A skin lesion imaged with a dermatoscope.
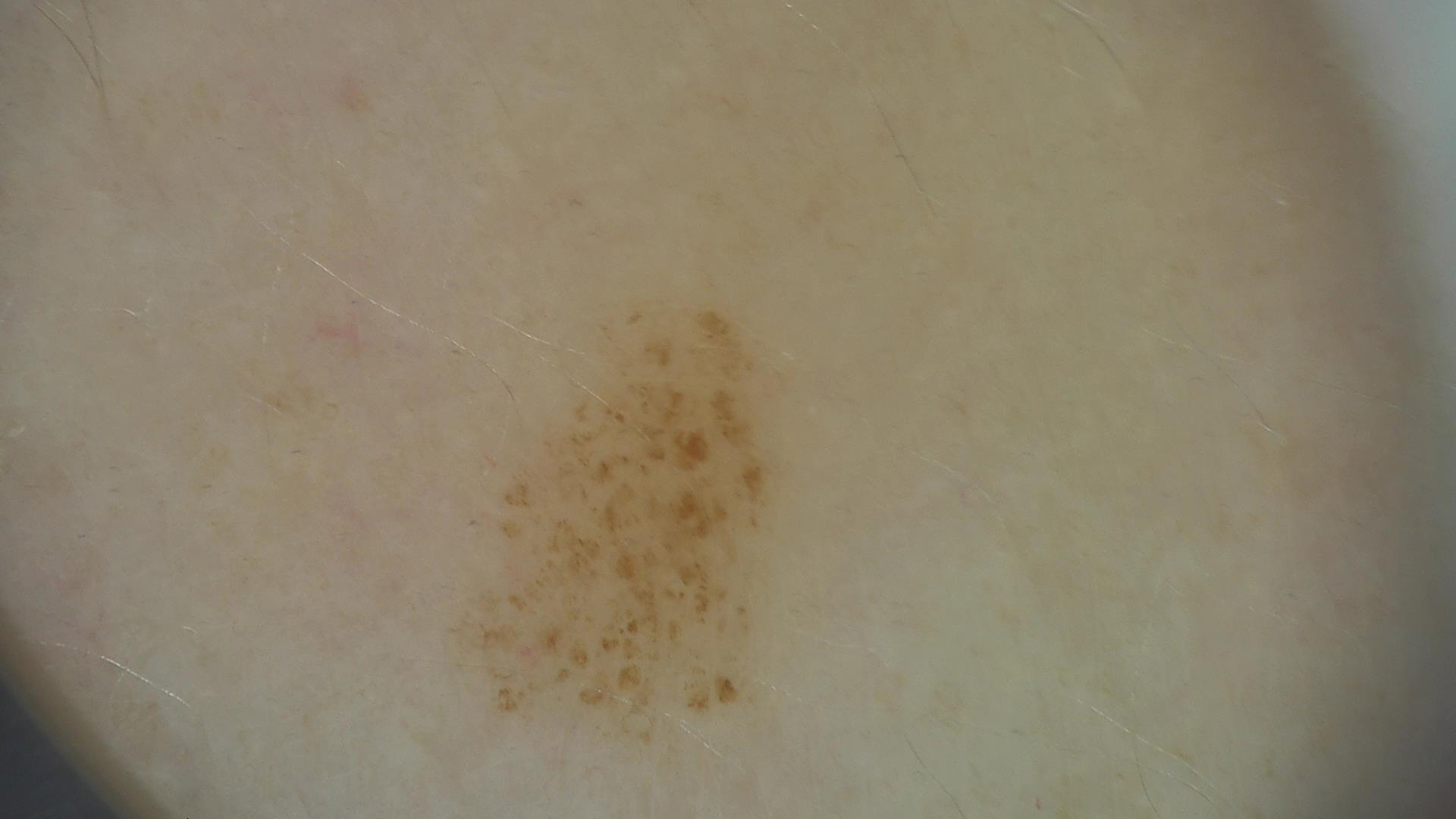The diagnostic label was a benign lesion — a dysplastic junctional nevus.